The top or side of the foot is involved, close-up view — 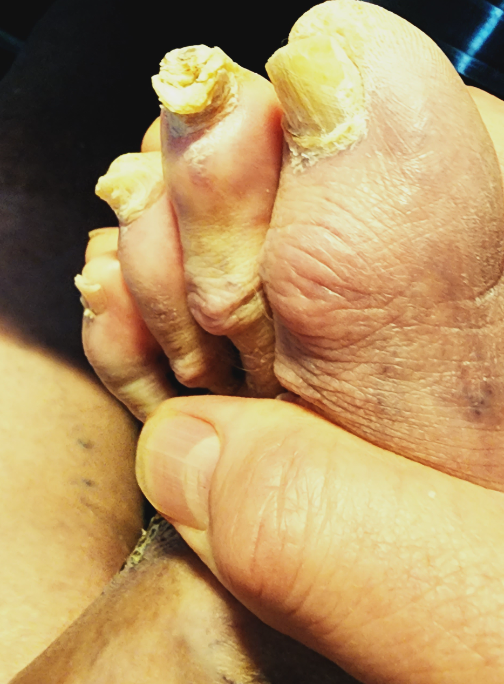Clinical context:
Present for more than five years. Texture is reported as raised or bumpy. The patient reports bothersome appearance. The patient considered this a nail problem.
Assessment:
Three independent reviewers: the primary impression is Onychomycosis; less probable is Psoriasis; a remote consideration is Pachyonychia congenita; less likely is Lichen planus/lichenoid eruption.